Female patient, age 18–29; the lesion involves the top or side of the foot; a close-up photograph.
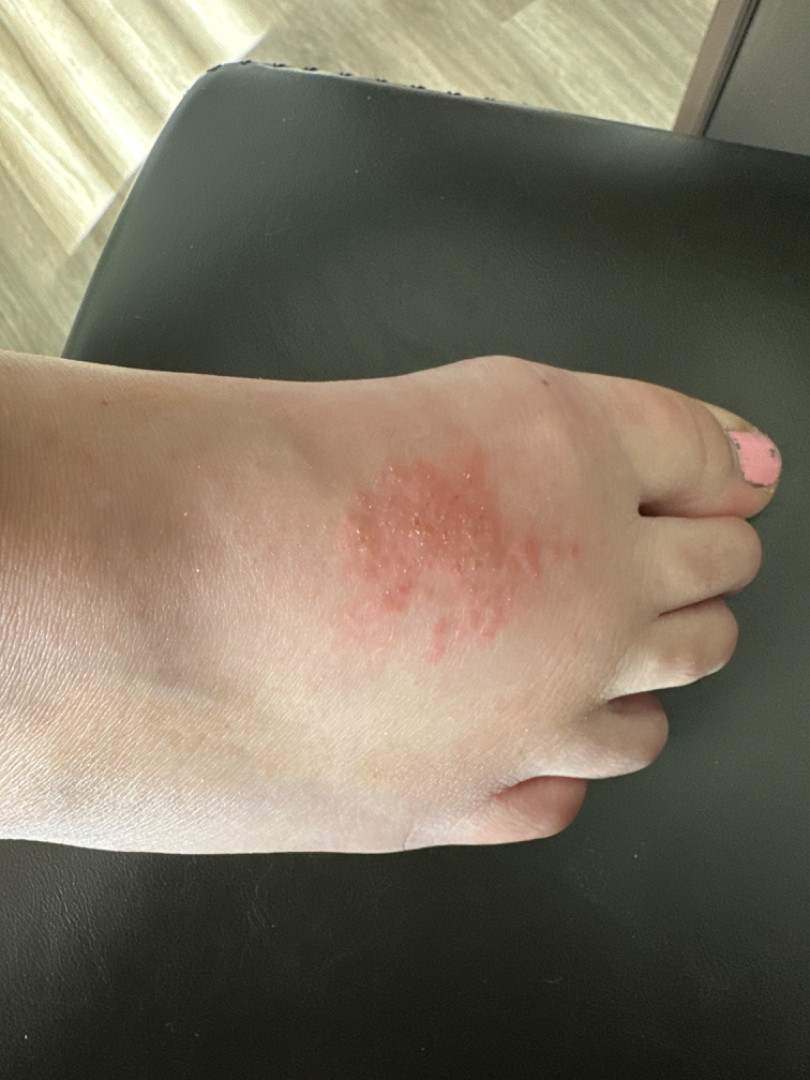<report>
<differential>
  <leading>Allergic Contact Dermatitis</leading>
  <considered>Eczema</considered>
</differential>
</report>